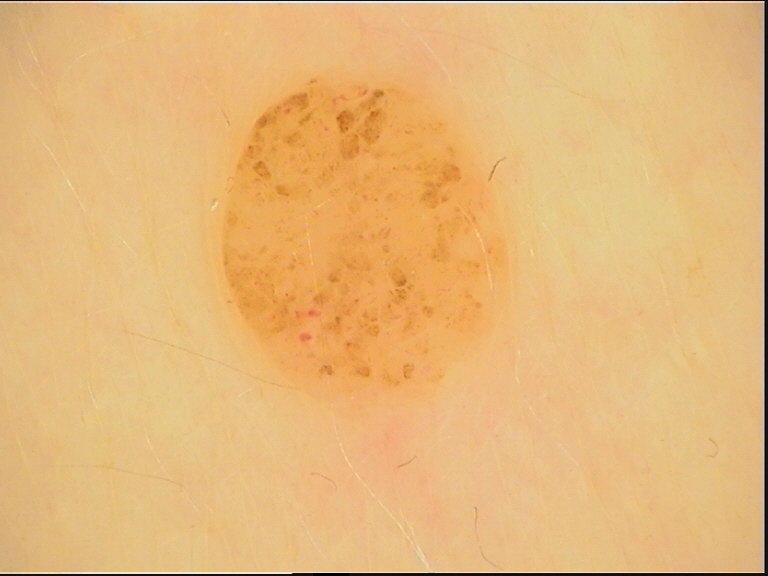imaging = dermoscopy; category = banal; diagnosis = compound nevus (expert consensus).